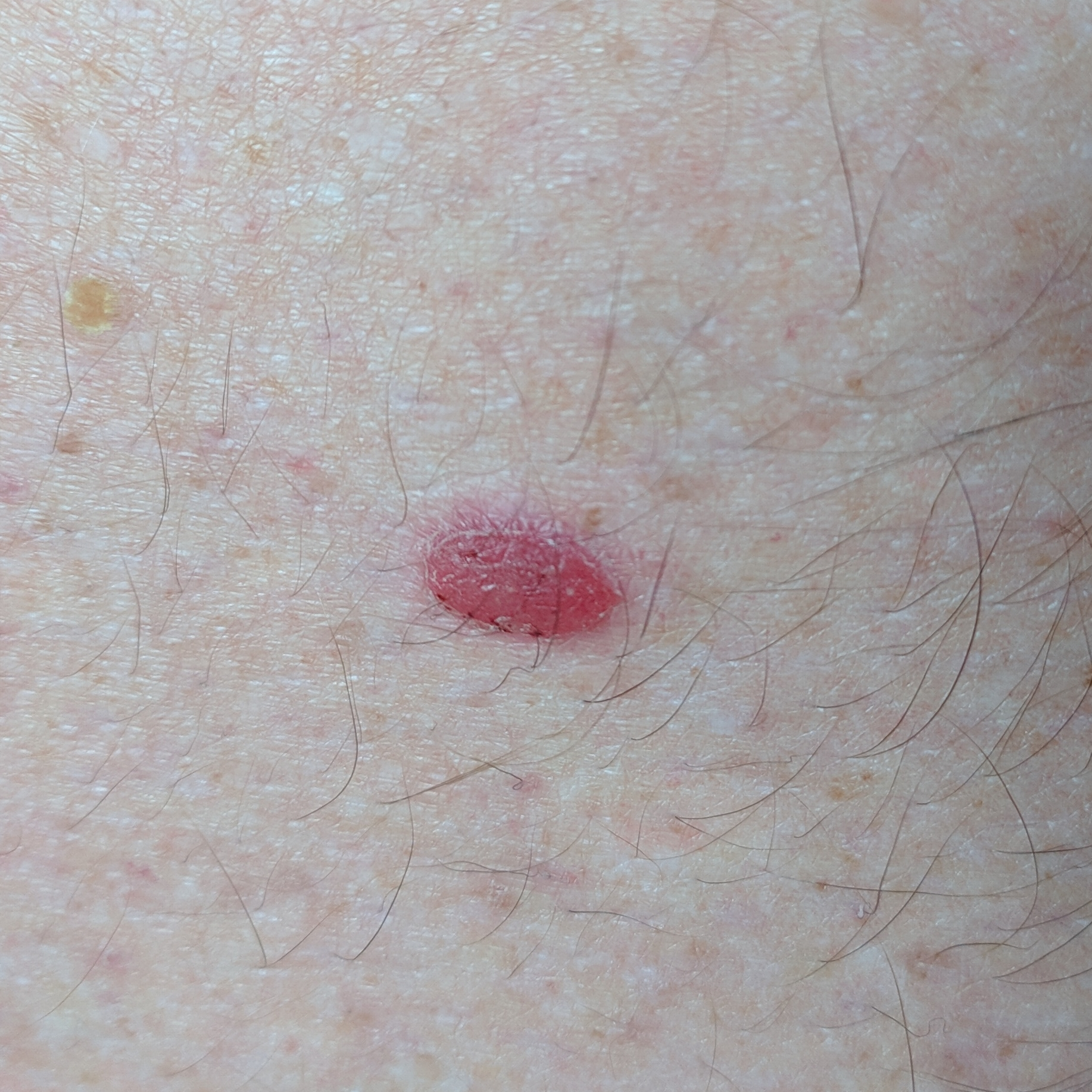* patient · male, in their 60s
* skin type · I
* image · smartphone clinical photo
* exposures · tobacco use, alcohol use, pesticide exposure
* site · the abdomen
* lesion diameter · approx. 10 × 7 mm
* patient-reported symptoms · growth, pain, itching, change in appearance, bleeding, elevation
* pathology · squamous cell carcinoma (biopsy-proven)